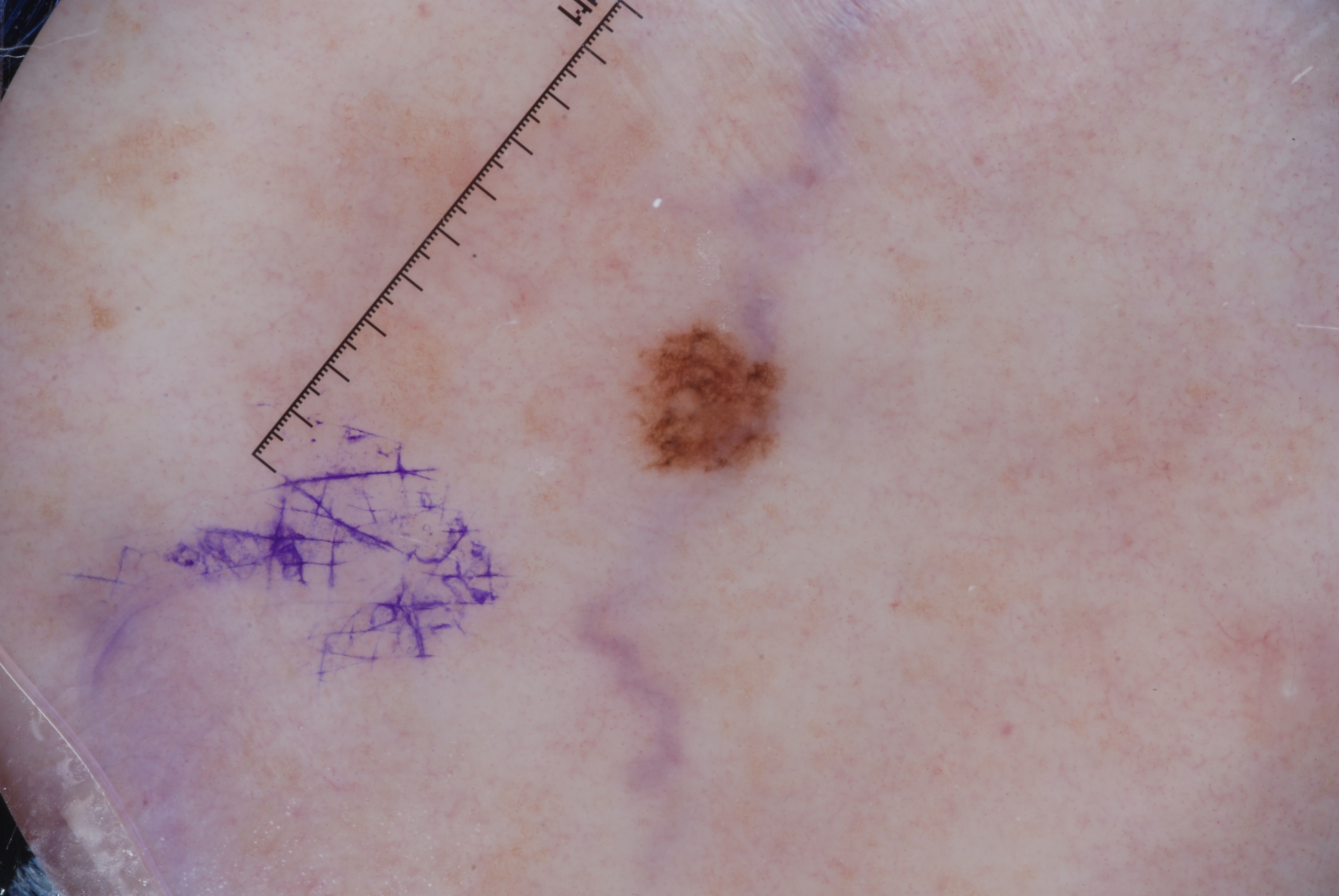Findings: This is a dermoscopic photograph of a skin lesion. The subject is a female aged 83 or older. As (left, top, right, bottom), the lesion is bounded by <bbox>638, 322, 784, 476</bbox>. Dermoscopic assessment notes pigment network; no milia-like cysts, negative network, or streaks. Conclusion: Clinically diagnosed as a melanocytic nevus, a benign lesion.